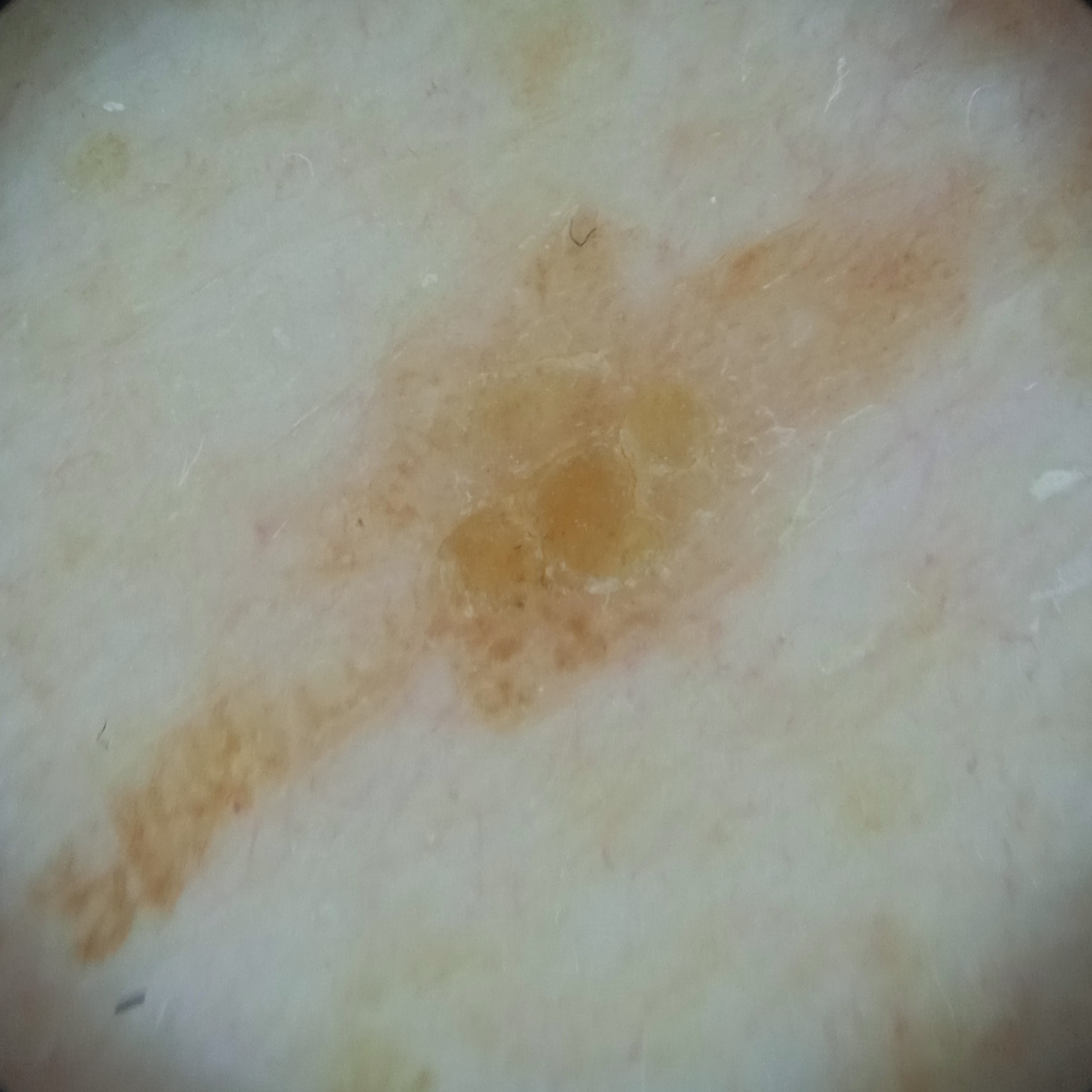<lesion>
<image>dermoscopy</image>
<sun_reaction>skin reddens with sun exposure</sun_reaction>
<patient>
<age>83</age>
<sex>male</sex>
</patient>
<lesion_location>the back</lesion_location>
<lesion_size>
<diameter_mm>16.4</diameter_mm>
</lesion_size>
<diagnosis>
<name>seborrheic keratosis</name>
<malignancy>benign</malignancy>
</diagnosis>
</lesion>